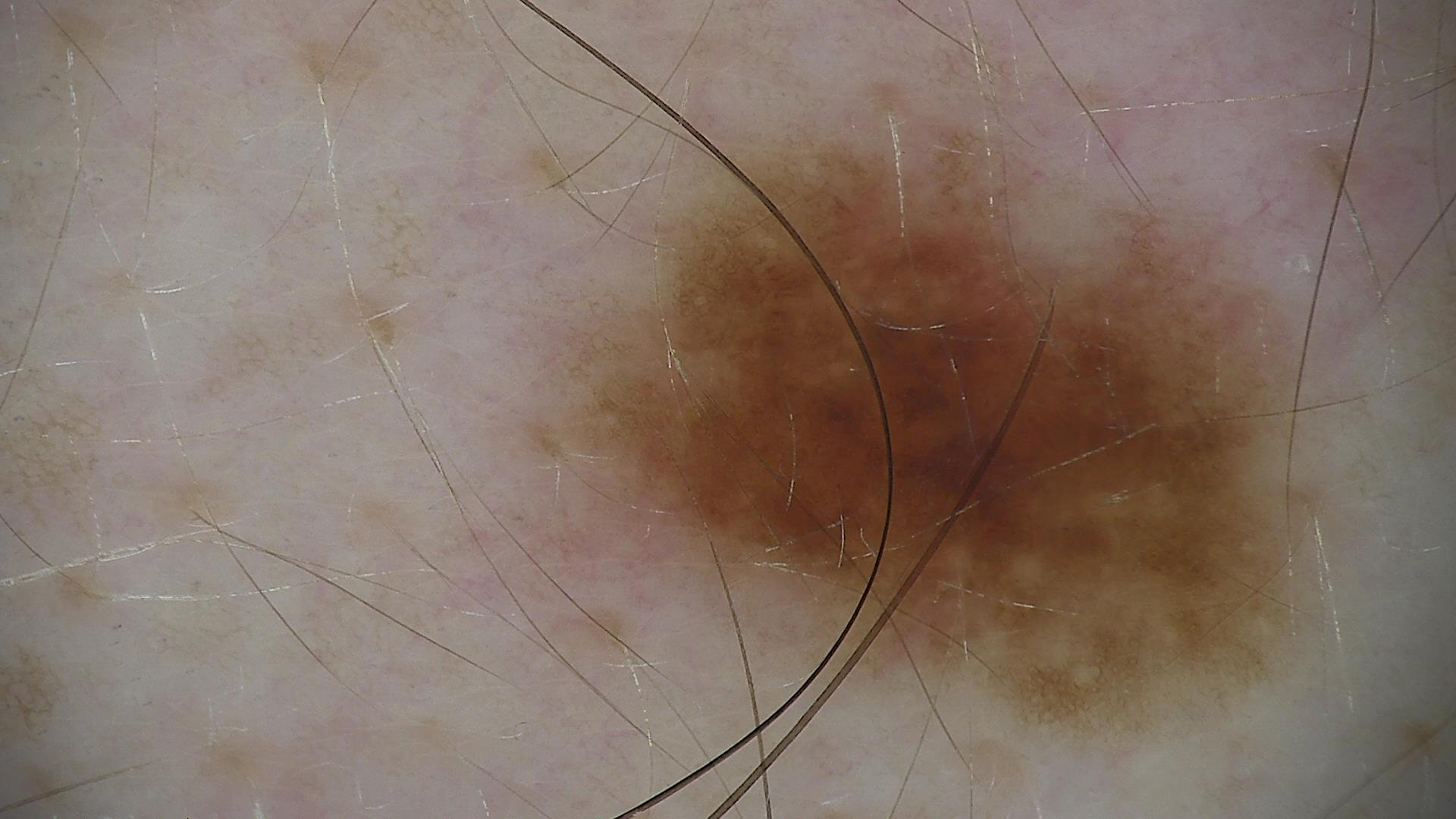Conclusion: The diagnosis was a dysplastic junctional nevus.